Texture is reported as flat. The lesion involves the back of the torso. Symptoms reported: itching and bothersome appearance. Fitzpatrick phototype II; lay graders estimated a Monk Skin Tone of 4. Reported duration is less than one week. An image taken at a distance. The patient considered this a rash.
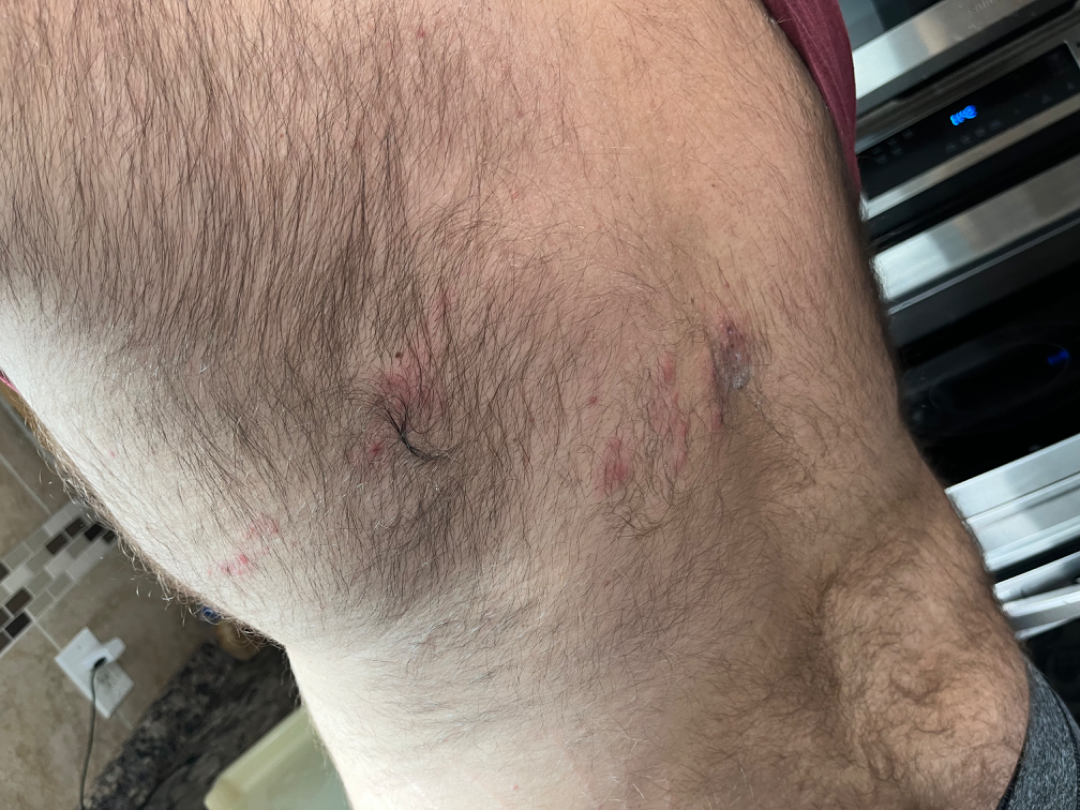A single dermatologist reviewed the case: in keeping with Herpes Zoster.